A skin lesion imaged with a dermatoscope.
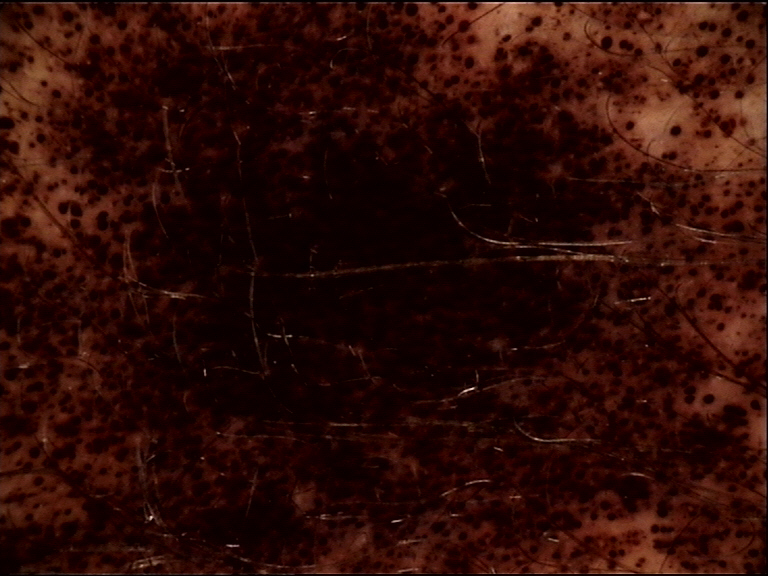This is a banal lesion. The diagnostic label was a congenital compound nevus.